The photograph is a close-up of the affected area; the arm is involved; male patient, age 18–29; the lesion is described as raised or bumpy; the condition has been present for one to four weeks; the patient considered this a rash; the lesion is associated with itching and bothersome appearance: 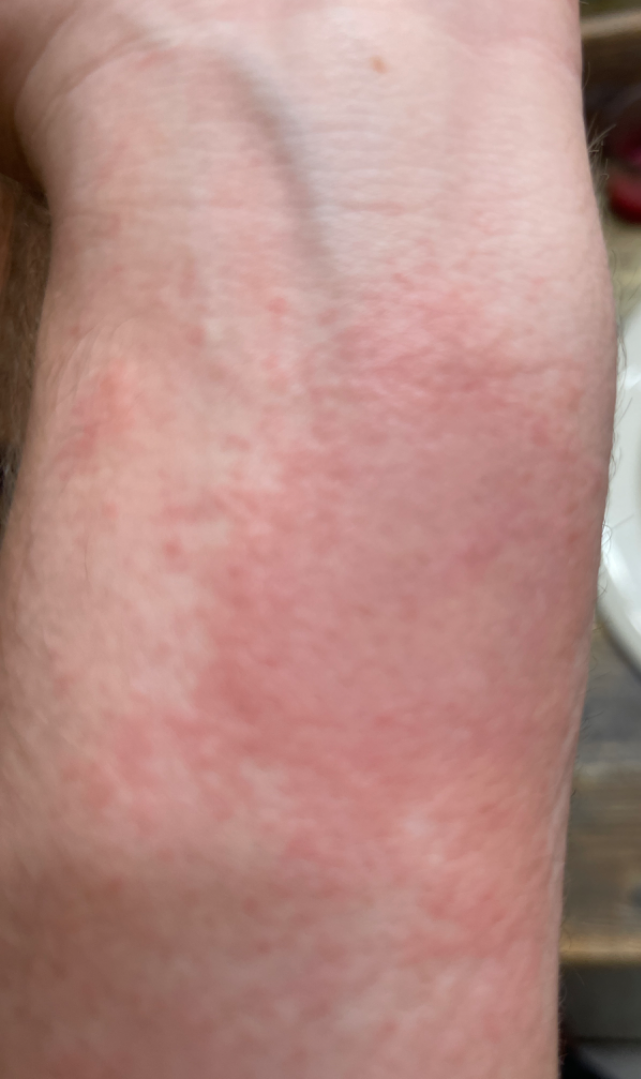Single-reviewer assessment: favoring Allergic Contact Dermatitis; an alternative is Tinea; also raised was Eczema.